A dermoscopic close-up of a skin lesion: 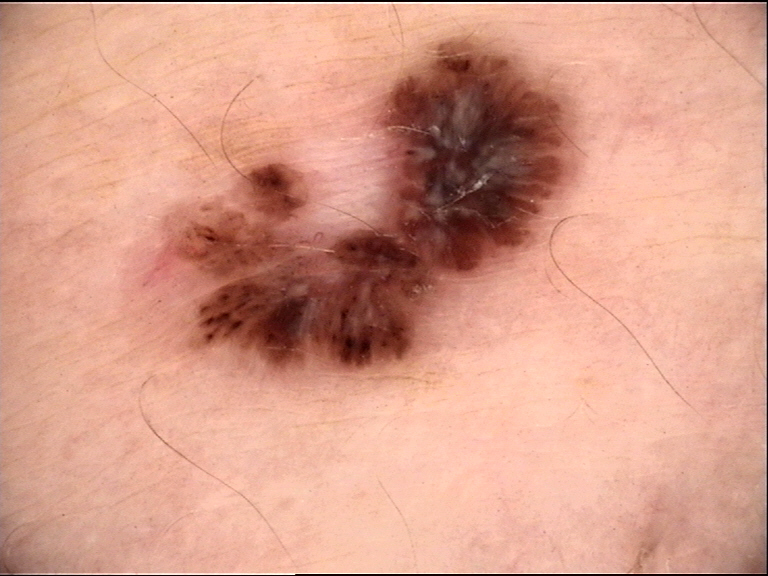Histopathology confirmed a keratinocytic lesion — a basal cell carcinoma.